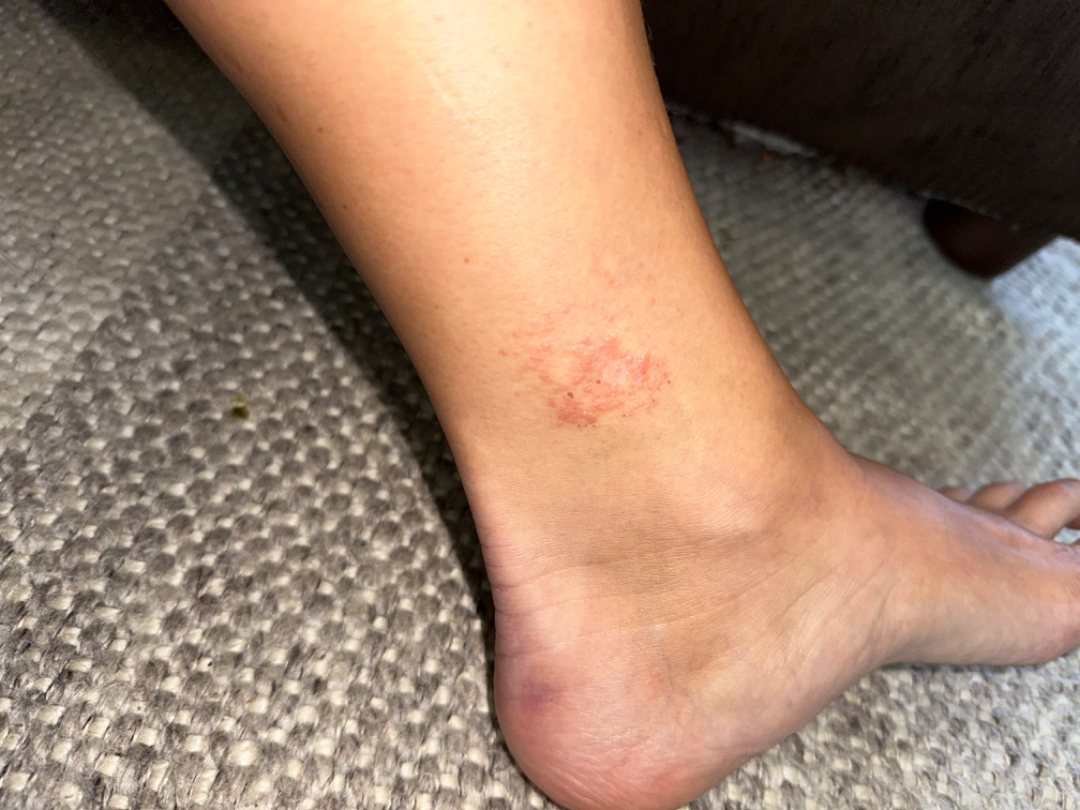Notes:
* self-categorized as: a rash
* affected area: leg
* framing: at a distance
* reported symptoms: bothersome appearance and itching
* constitutional symptoms: none reported
* dermatologist impression: consistent with Eczema